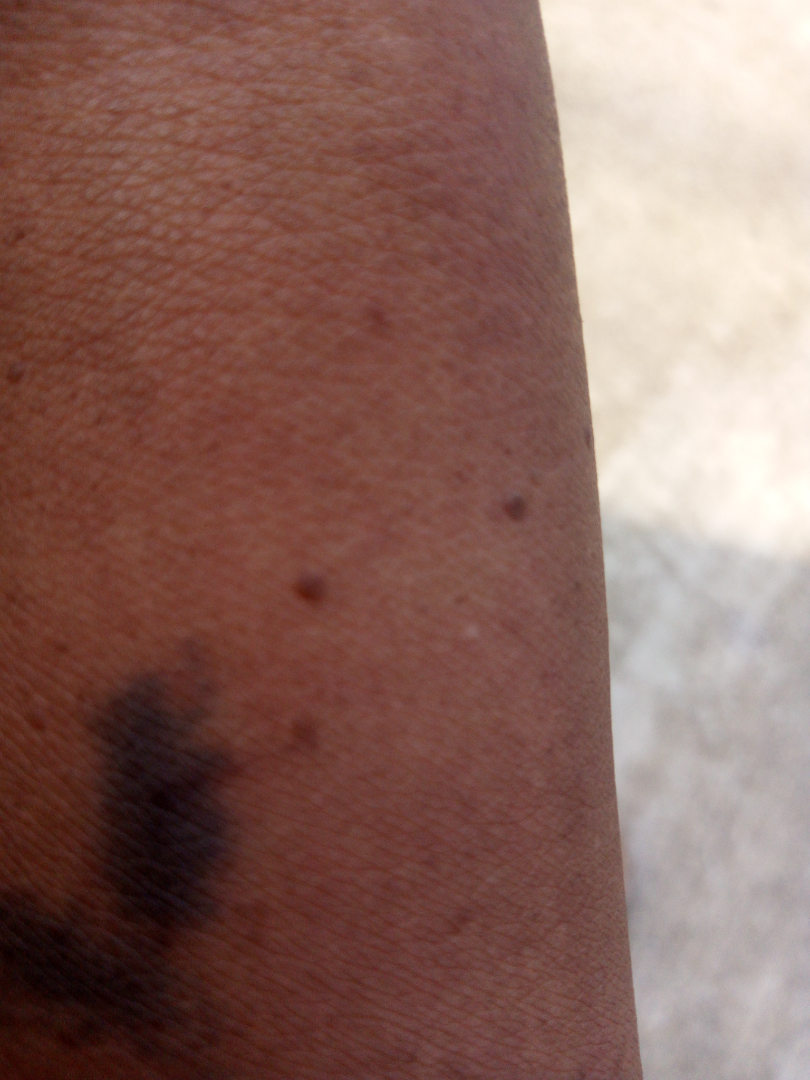assessment: indeterminate from the photograph | body site: leg and arm | history: one to three months | lesion symptoms: burning, pain, itching, bothersome appearance, darkening and enlargement | shot type: close-up | texture: flat and raised or bumpy.